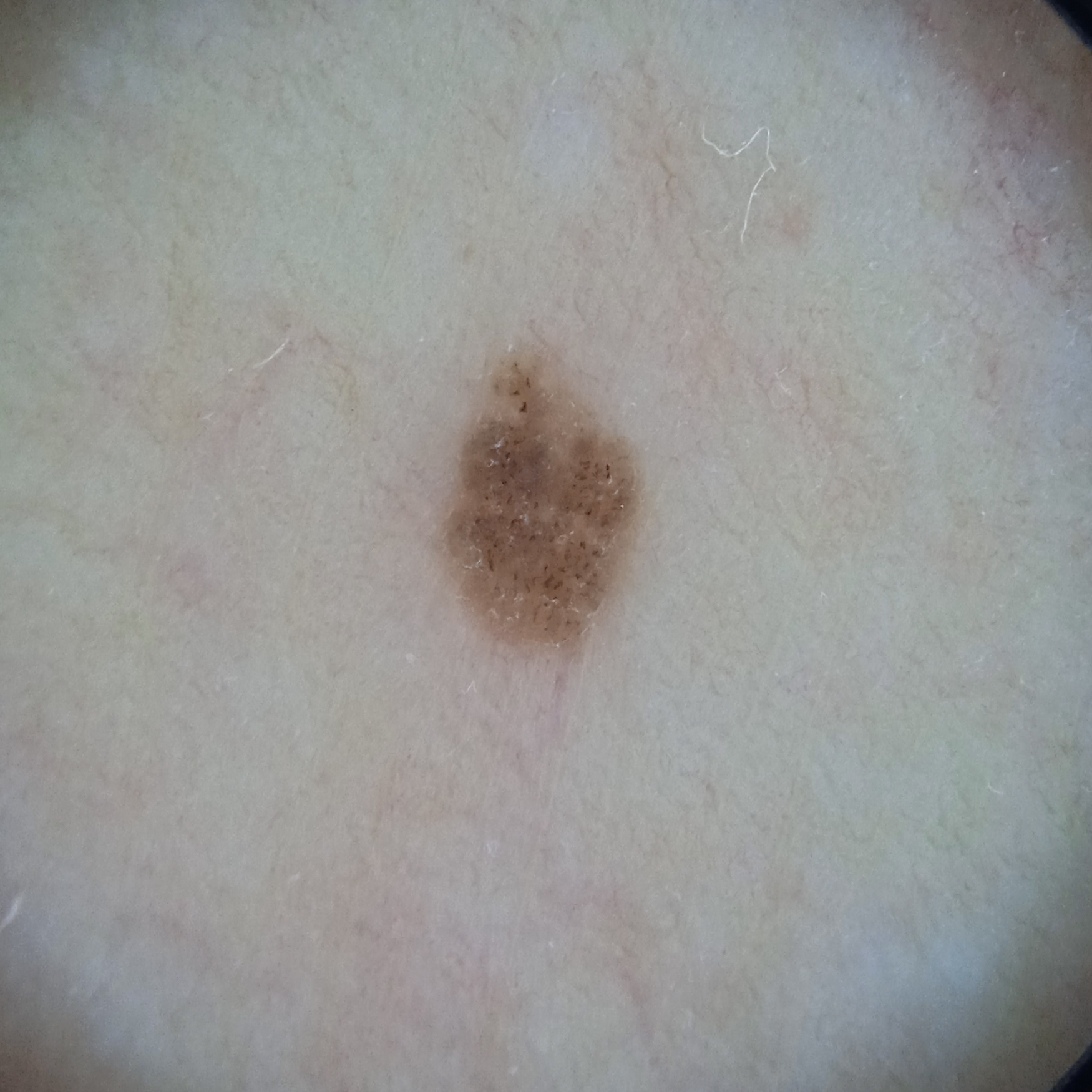| feature | finding |
|---|---|
| sun reaction | skin tans without first burning |
| image type | dermoscopic image |
| patient | female, 60 years old |
| relevant history | a personal history of cancer, a personal history of skin cancer, no immunosuppression |
| anatomic site | the torso |
| diameter | 3.4 mm |
| diagnostic label | melanocytic nevus (dermatologist consensus) |